Dermoscopy of a skin lesion: 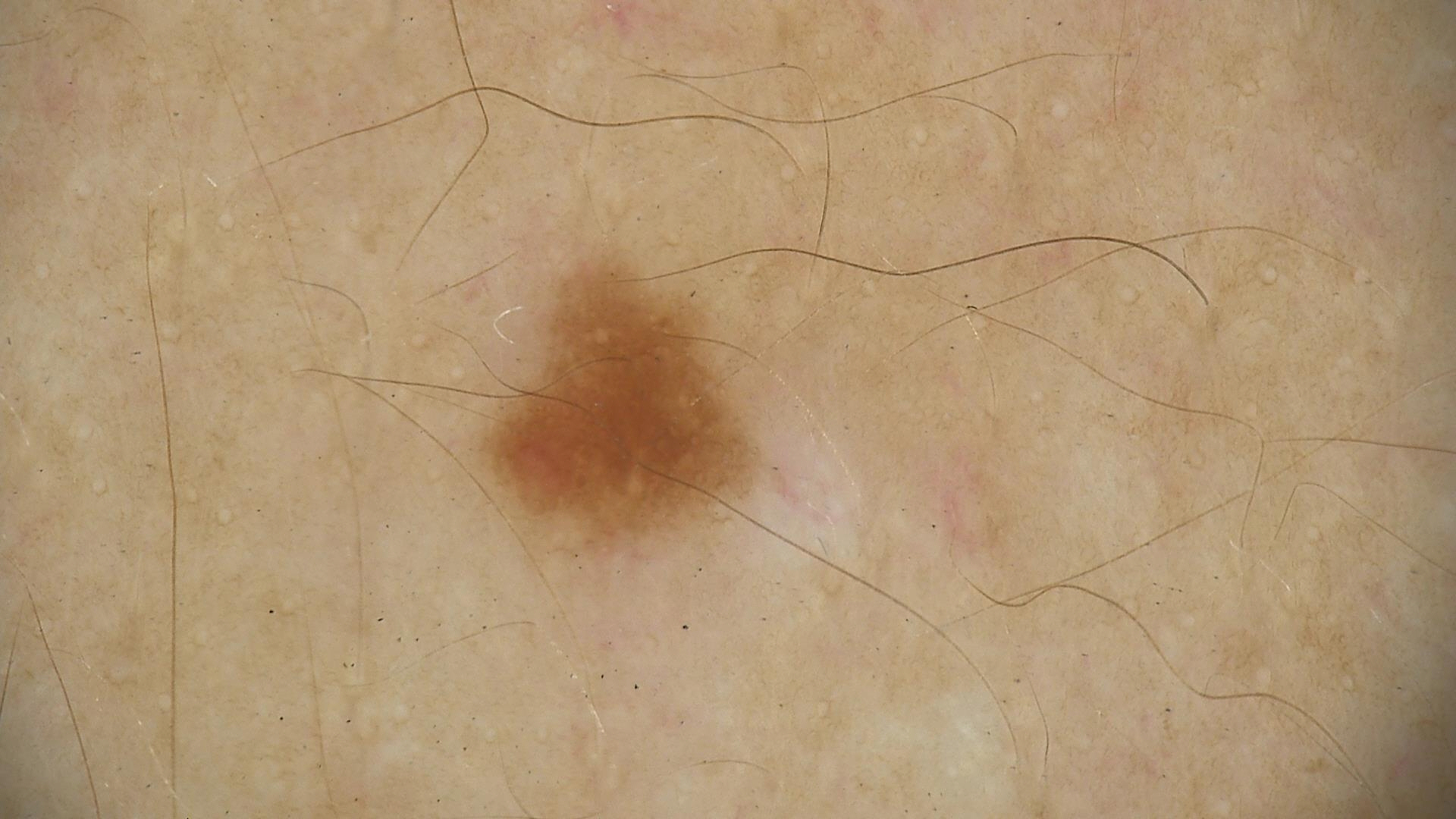Conclusion:
Consistent with a dysplastic junctional nevus.